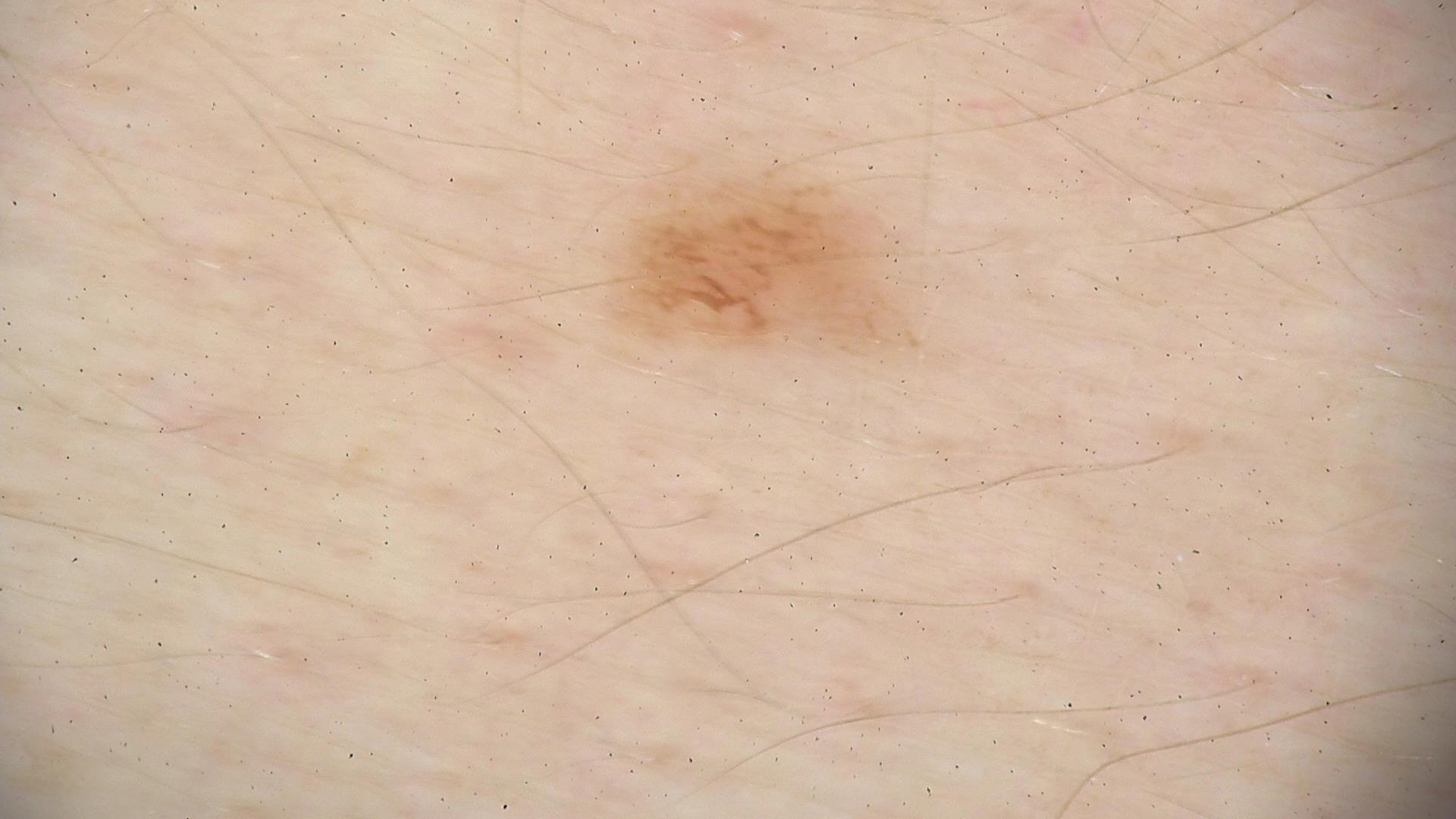A dermatoscopic image of a skin lesion.
The diagnosis was a dysplastic junctional nevus.